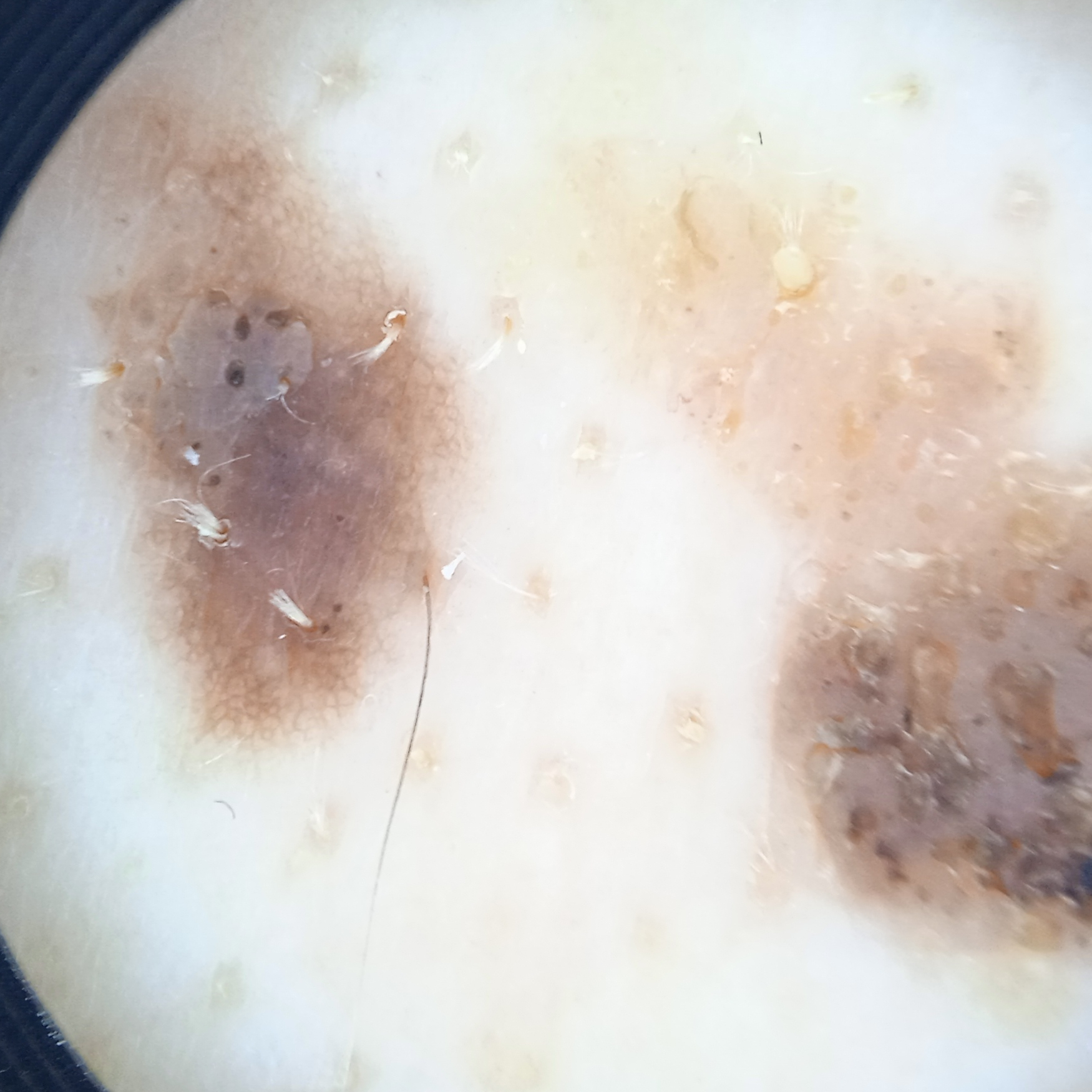| field | value |
|---|---|
| assessment | seborrheic keratosis (dermatologist consensus) |